An image taken at a distance. The patient is 18–29, female:
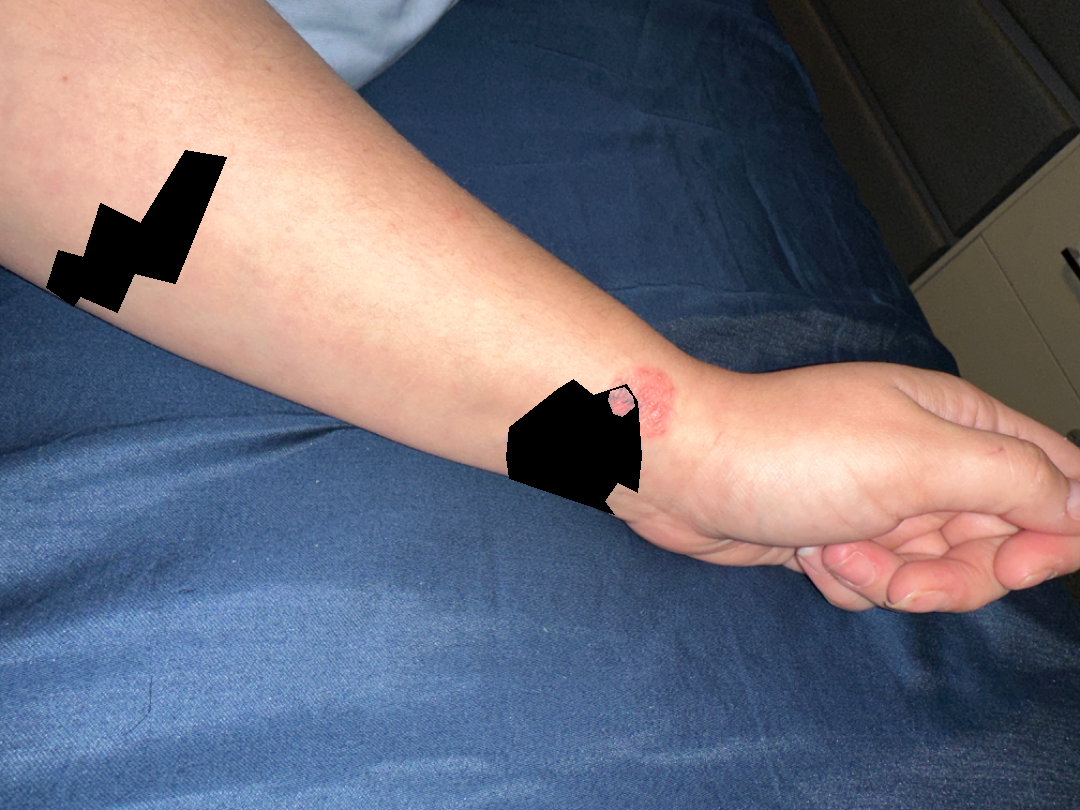The patient reports the lesion is raised or bumpy and rough or flaky.
The patient also reports chills, fatigue and joint pain.
Reported lesion symptoms include pain, enlargement, bothersome appearance, itching and burning.
The patient considered this a rash.
On remote review of the image: the differential includes Eczema, Psoriasis and Allergic Contact Dermatitis, with no clear leading consideration.